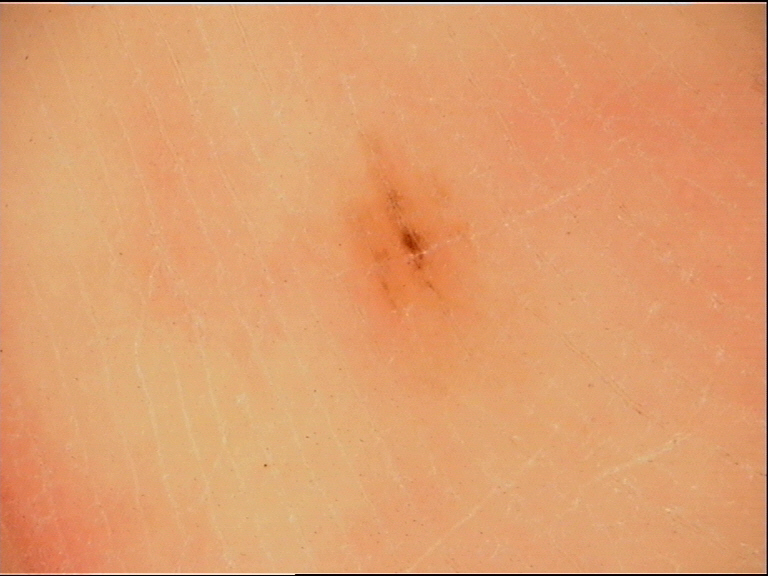A dermatoscopic image of a skin lesion.
The architecture is that of a banal lesion.
Consistent with an acral junctional nevus.